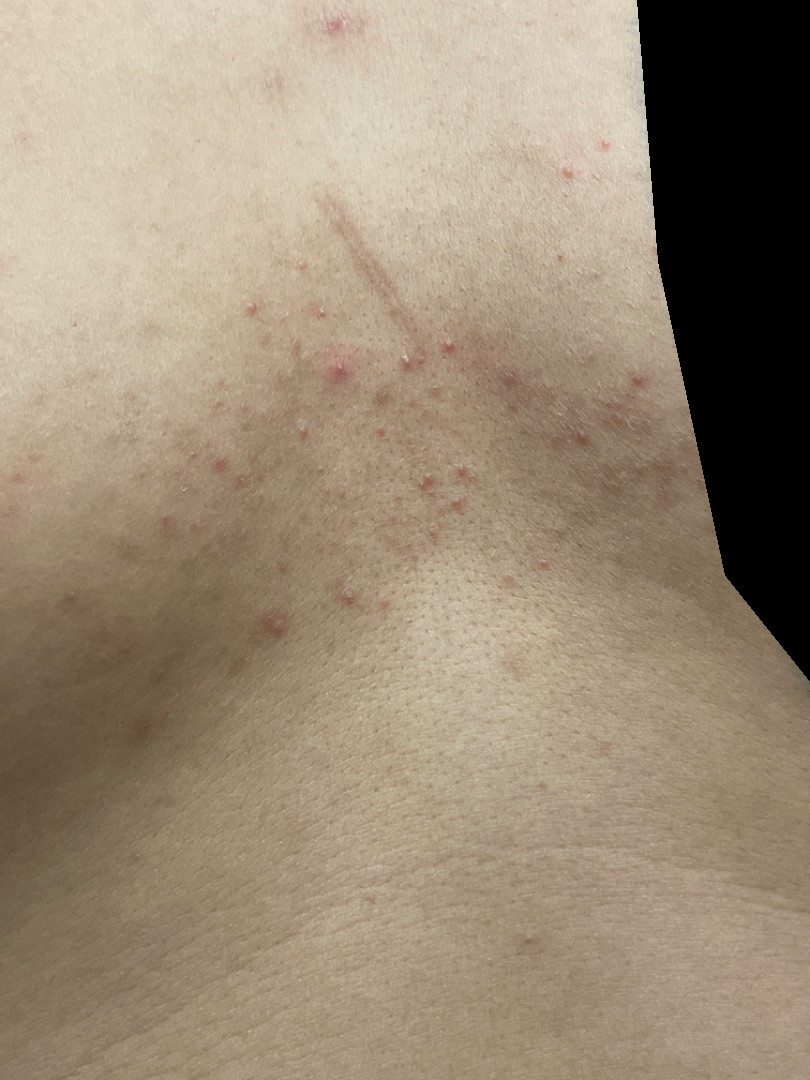{
  "skin_tone": {
    "fitzpatrick": "III",
    "monk_skin_tone": [
      1,
      3
    ]
  },
  "shot_type": "at an angle",
  "patient": "male, age 30–39",
  "body_site": [
    "back of the torso",
    "front of the torso"
  ],
  "texture": "raised or bumpy",
  "duration": "more than one year",
  "patient_category": "a rash",
  "differential": {
    "leading": [
      "Folliculitis"
    ],
    "considered": [
      "Acne"
    ],
    "unlikely": [
      "Grover's disease"
    ]
  }
}